Female patient, age 18–29; the lesion involves the back of the torso and front of the torso; the photograph is a close-up of the affected area: 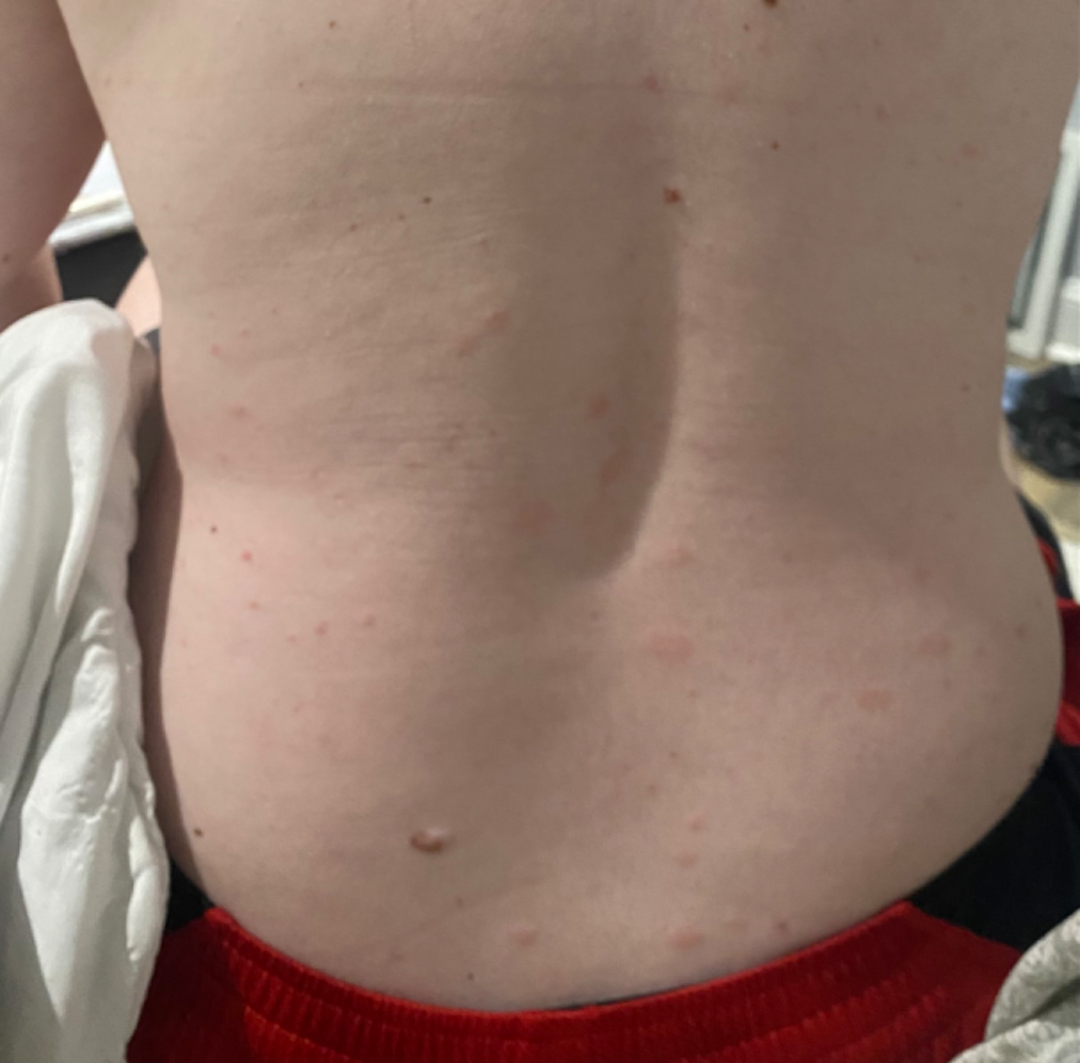patient describes the issue as — a rash
described texture — raised or bumpy and rough or flaky
skin tone — human graders estimated Monk Skin Tone 2
systemic symptoms — none reported
symptoms — enlargement and bothersome appearance
differential diagnosis — favoring Pityriasis rosea; an alternative is Psoriasis; a more distant consideration is Eczema